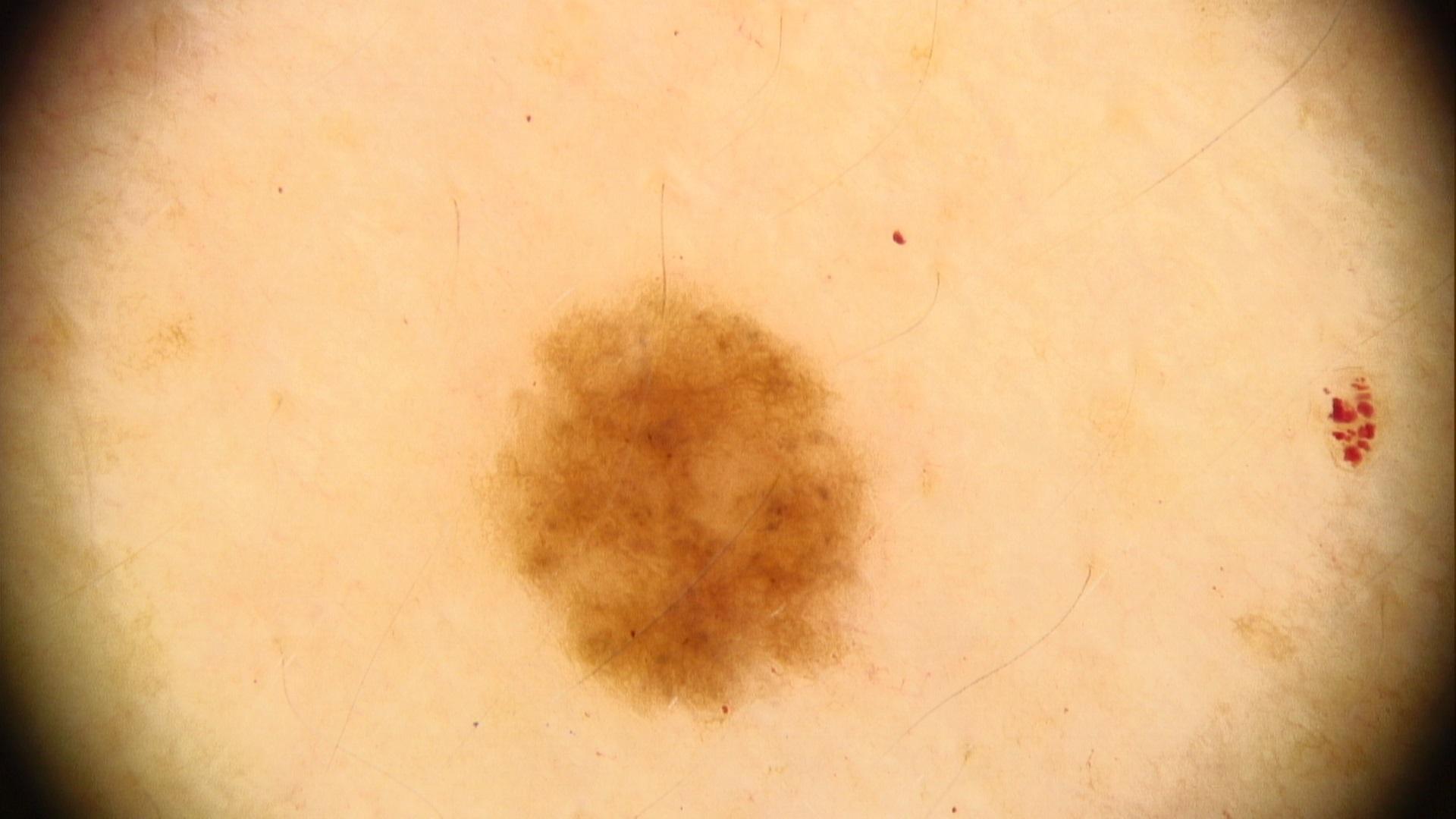modality: contact-polarized dermoscopy; skin type: IV; assessment: Nevus.